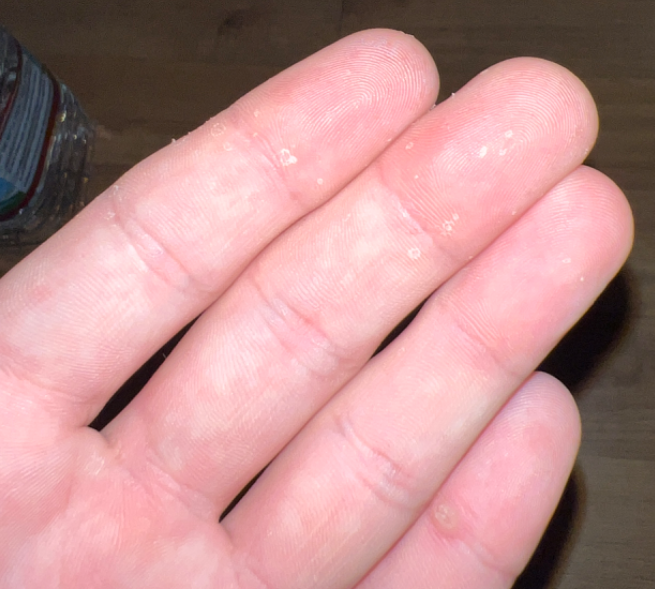The case was indeterminate on photographic review. The patient indicates the lesion is rough or flaky. The patient considered this acne. An image taken at a distance. The lesion involves the palm. The contributor is a male aged 30–39.